A dermoscopic image of a skin lesion:
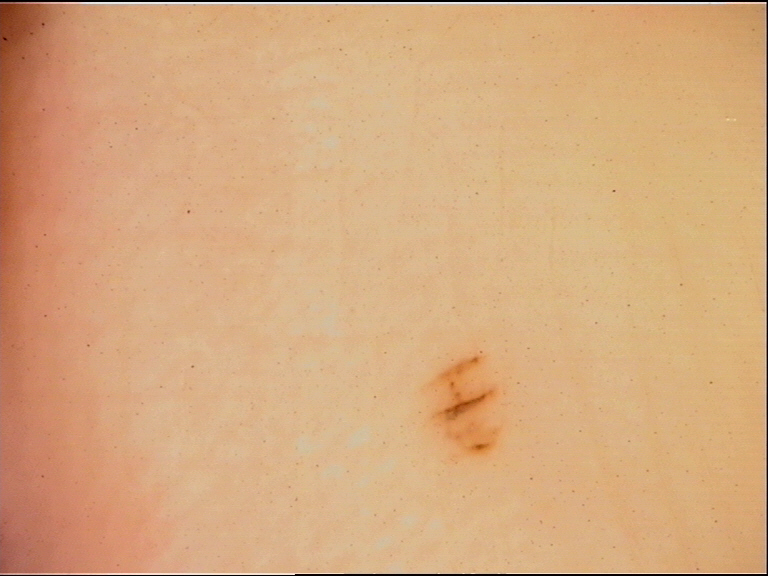Conclusion:
The diagnostic label was an acral dysplastic junctional nevus.